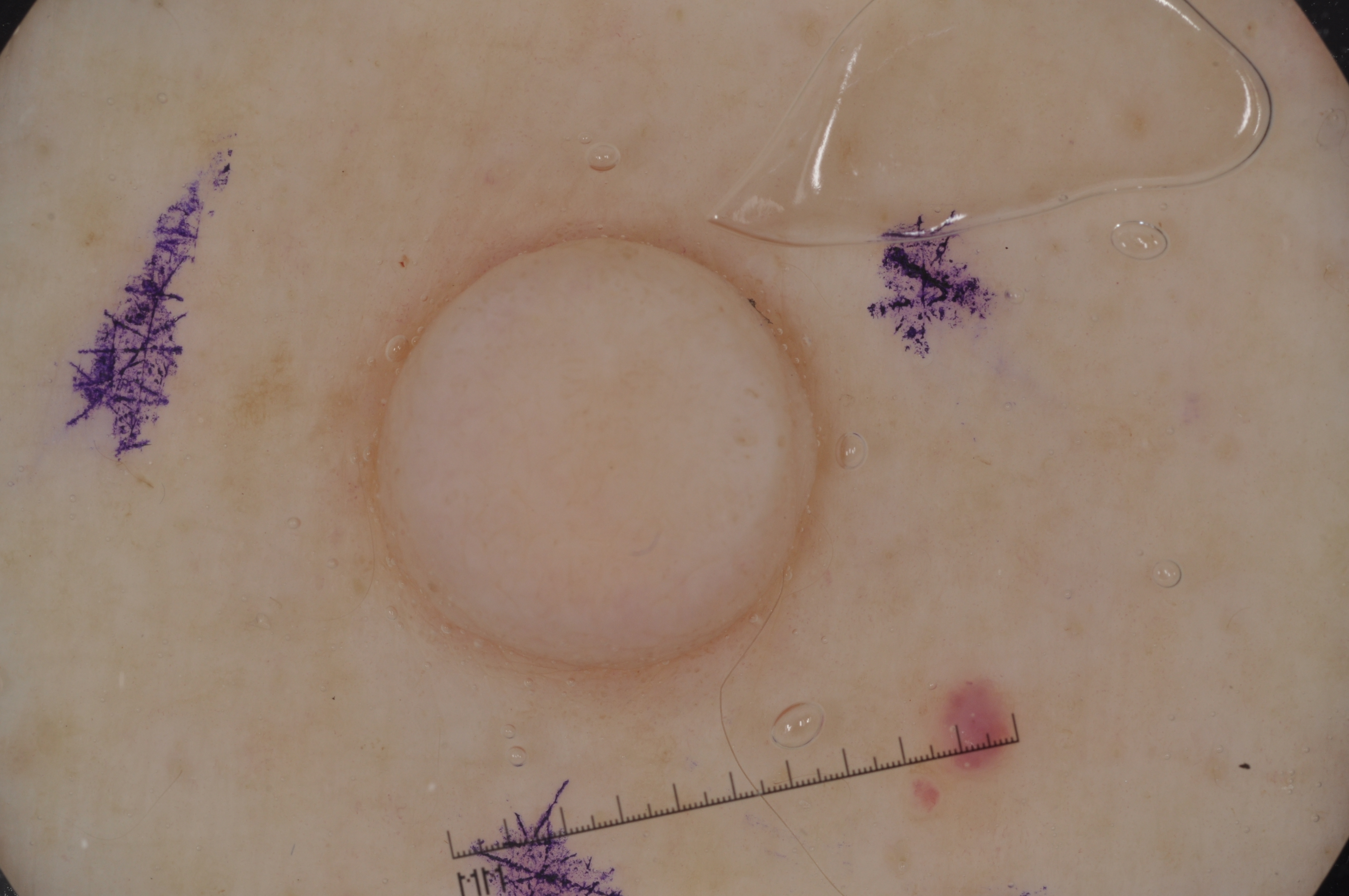Summary:
The patient is a male approximately 70 years of age. A dermoscopic image of a skin lesion. In (x1, y1, x2, y2) order, the lesion is located at 350/216/825/682. Dermoscopic assessment notes no negative network, streaks, pigment network, or milia-like cysts.
Conclusion:
The diagnostic assessment was a melanocytic nevus, a benign skin lesion.